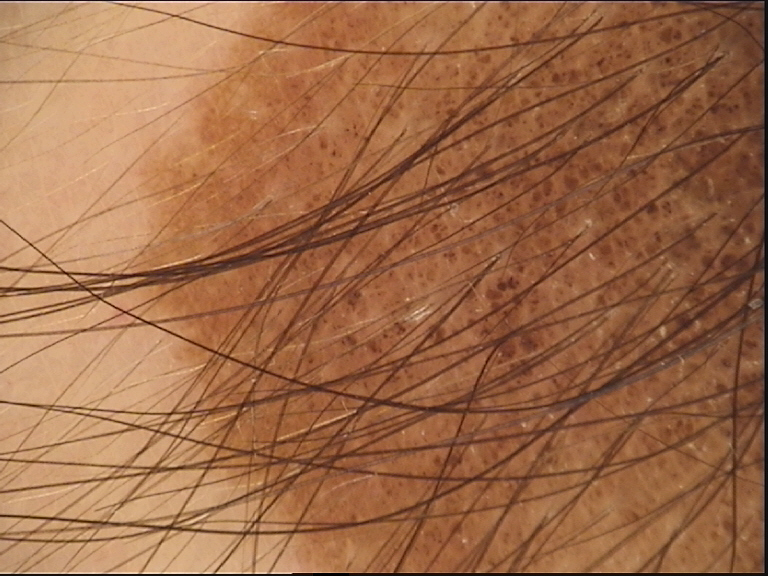Conclusion: Consistent with a congenital compound nevus.